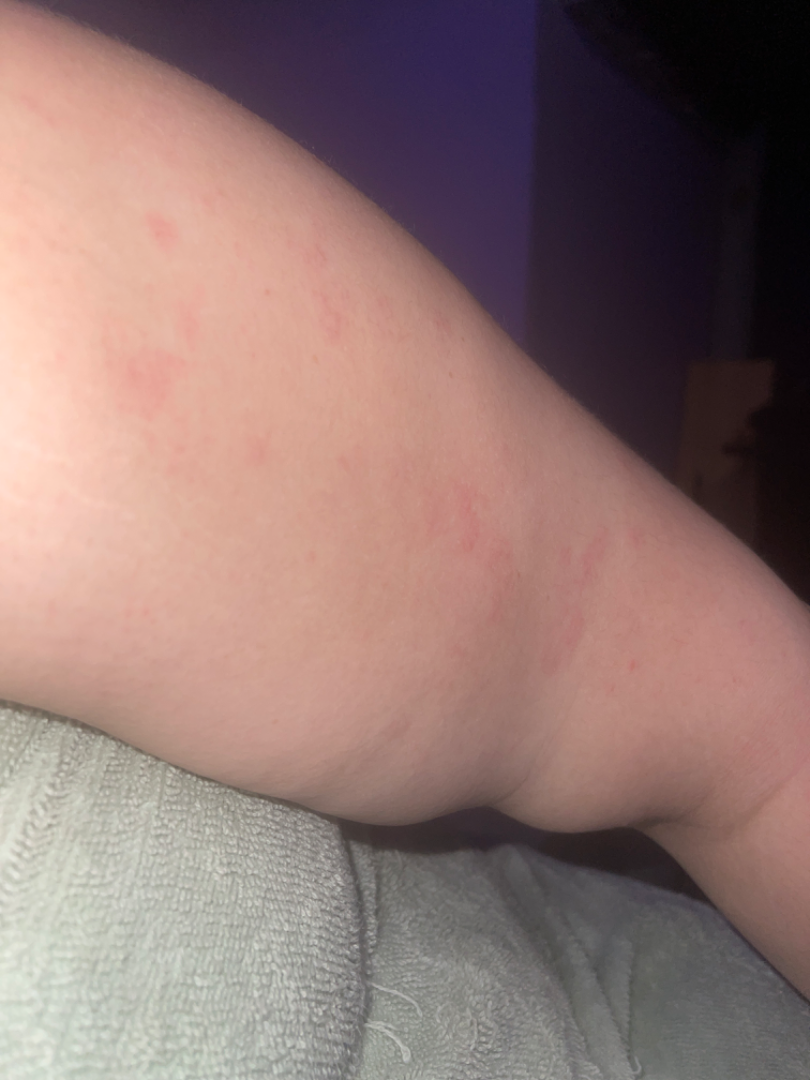Patient information:
The lesion involves the arm and front of the torso. The patient reports the lesion is rough or flaky and flat. Reported duration is one to three months. The patient considered this a rash. An image taken at an angle. FST II; human graders estimated 2 on the Monk Skin Tone. Reported lesion symptoms include itching and enlargement.
Review:
The reviewing panel's impression was: Allergic Contact Dermatitis (0.67); Urticaria (0.33).